A skin lesion imaged with a dermatoscope.
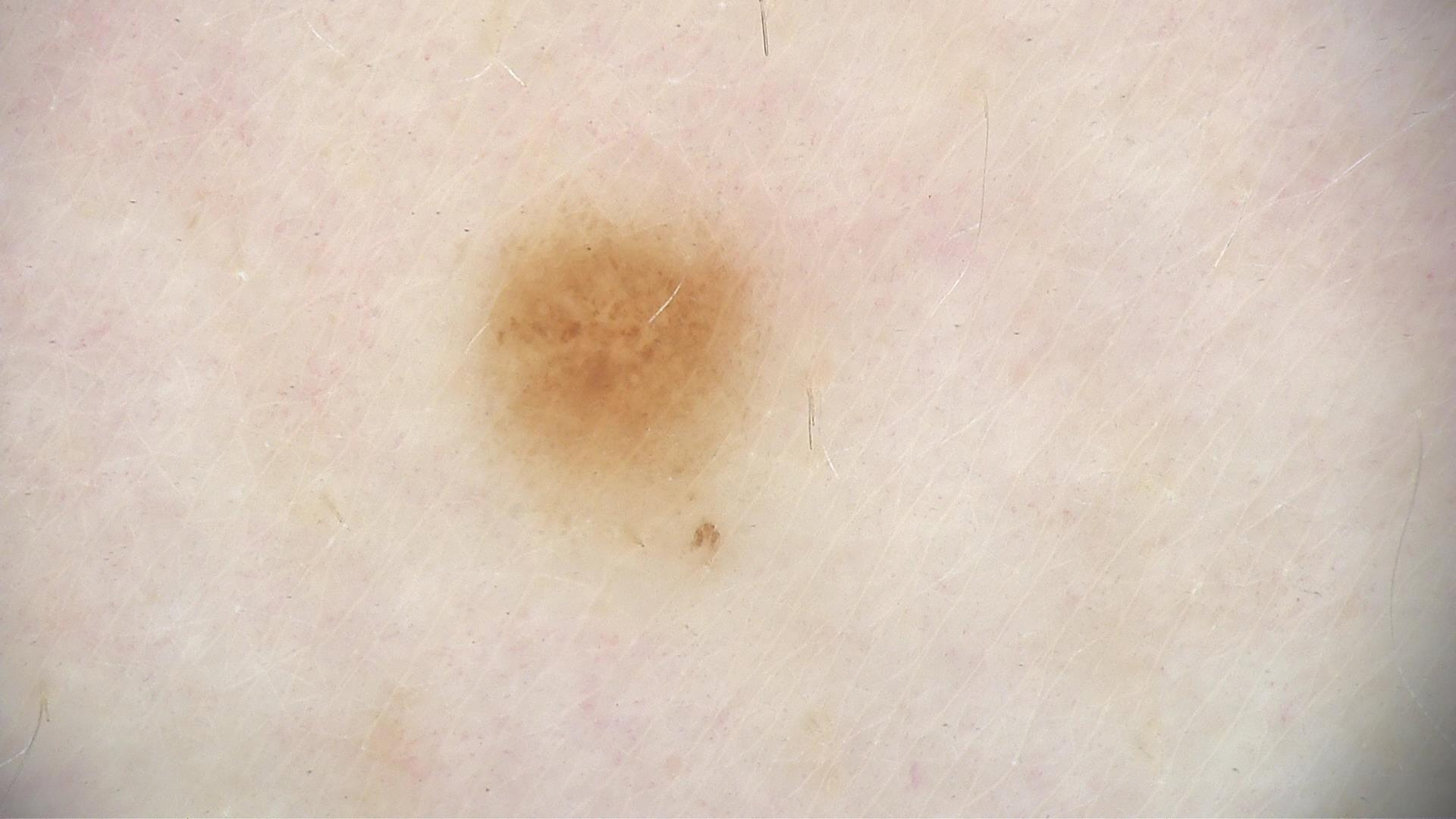Q: What is this lesion?
A: dysplastic junctional nevus (expert consensus)